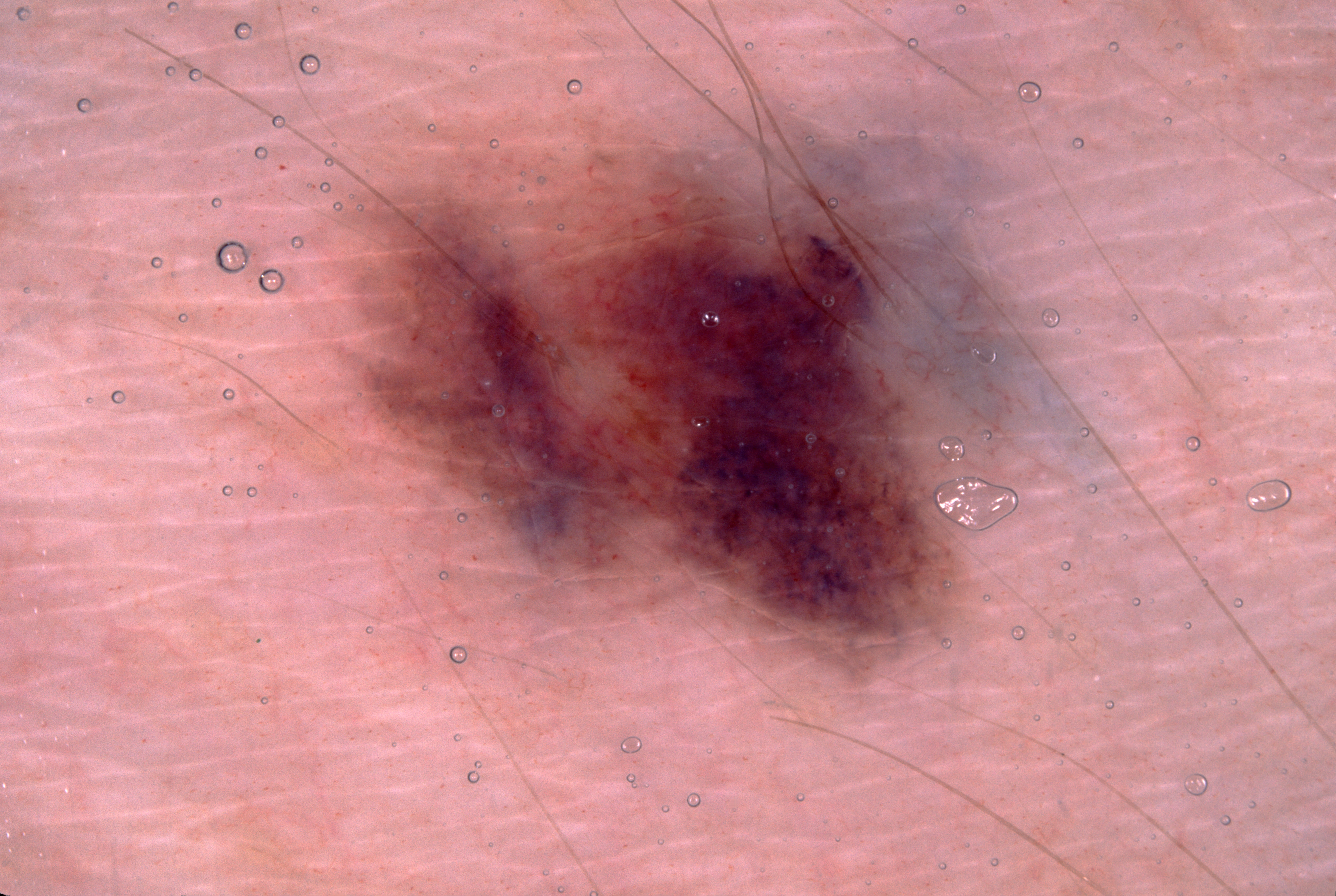A dermoscopic image of a skin lesion. With coordinates (x1, y1, x2, y2), the lesion's extent is [355, 140, 960, 651]. Diagnosed as a melanocytic nevus, a benign lesion.